Female contributor, age 50–59 · this image was taken at an angle:
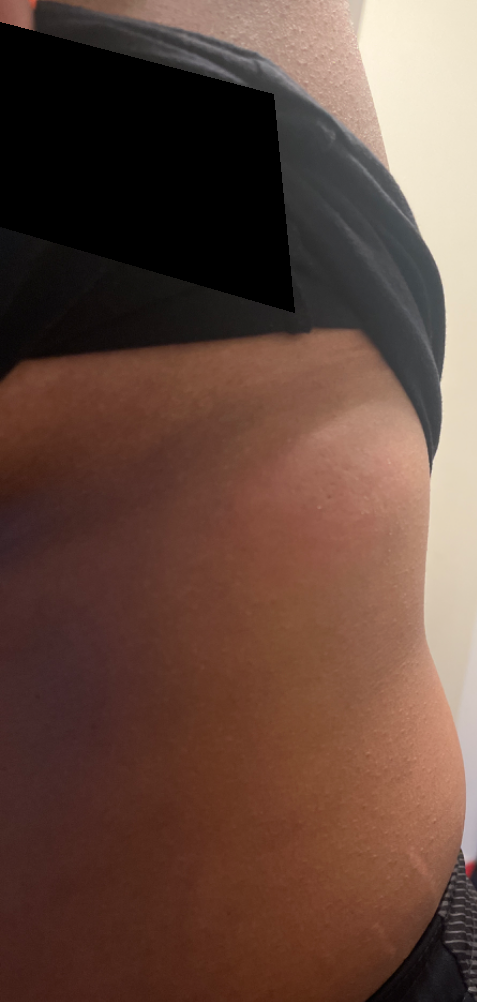Case summary:
* differential — three dermatologists independently reviewed the case: Urticaria and Erythema migrans were each considered, in no particular order; less likely is Allergic Contact Dermatitis